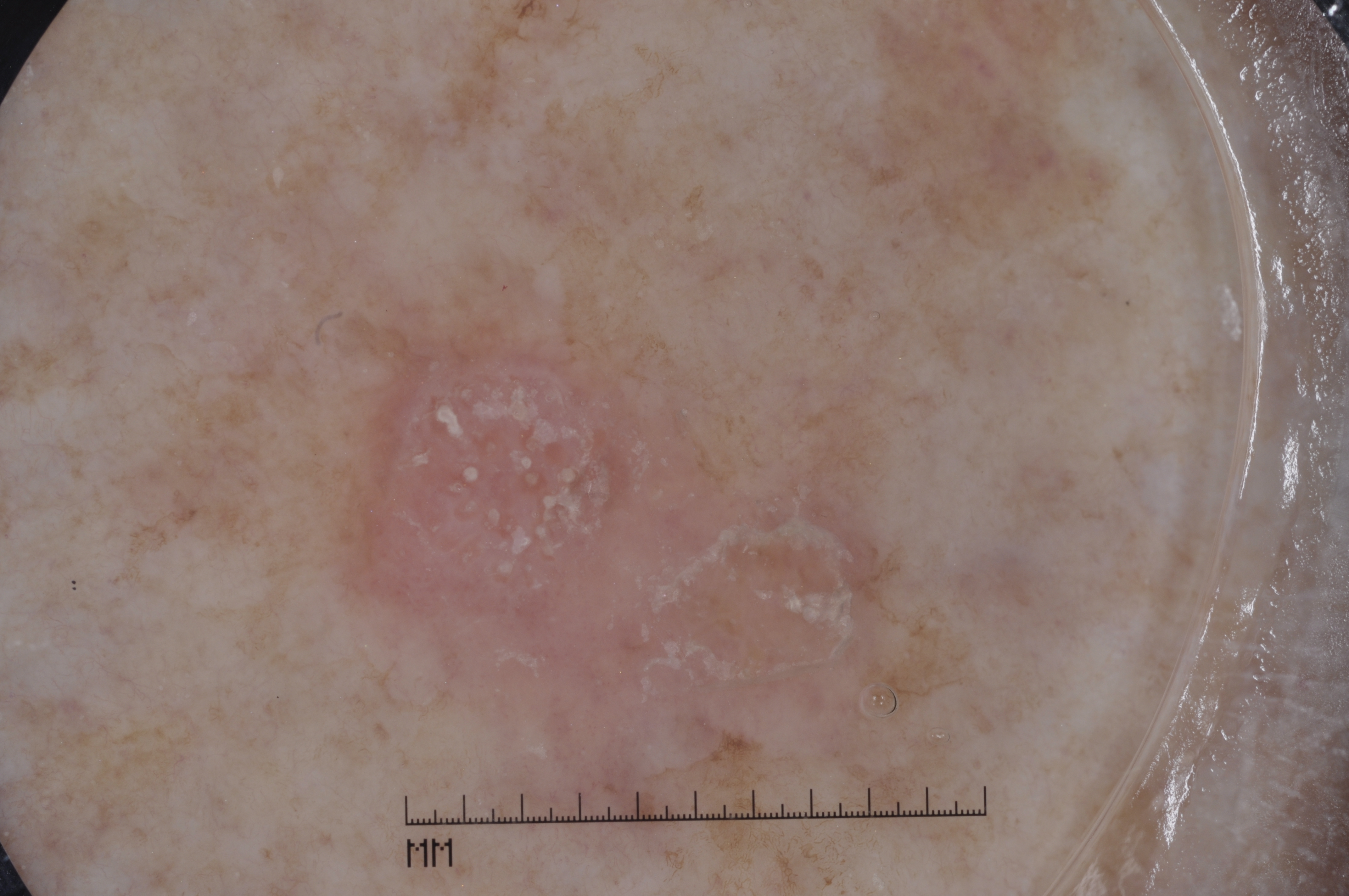Summary: A skin lesion imaged with a dermatoscope. A female subject, aged approximately 70. Dermoscopic assessment notes no milia-like cysts, streaks, negative network, or pigment network. The lesion is located at (347, 291, 963, 815). The lesion covers approximately 16% of the dermoscopic field. Assessment: Consistent with a seborrheic keratosis, a benign skin lesion.